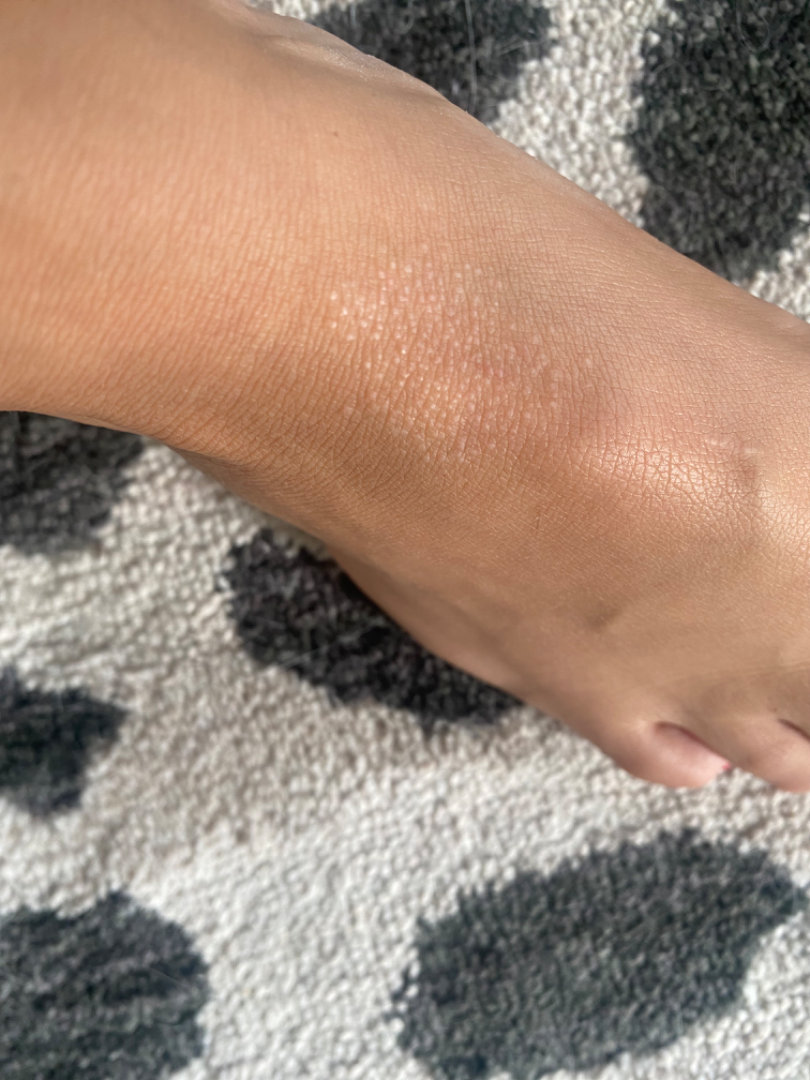Notes:
- body site — arm and top or side of the foot
- patient — female, age 18–29
- photo taken — close-up
- clinical impression — favoring Lichen nitidus